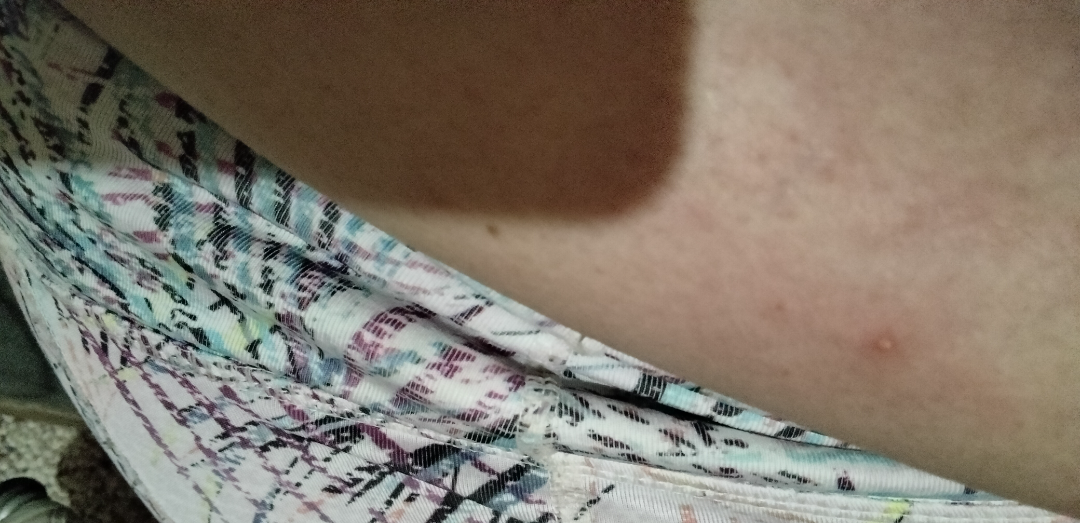No relevant systemic symptoms.
The lesion is associated with enlargement, itching and bothersome appearance.
Skin tone: Fitzpatrick phototype II.
Close-up view.
The patient notes the lesion is raised or bumpy.
The patient is a female aged 40–49.
Present for less than one week.
The front of the torso is involved.
Favoring Folliculitis; lower on the differential is Acne; a remote consideration is Infected eczema; less likely is Abscess.